A clinical photograph of a skin lesion · a subject 28 years old: 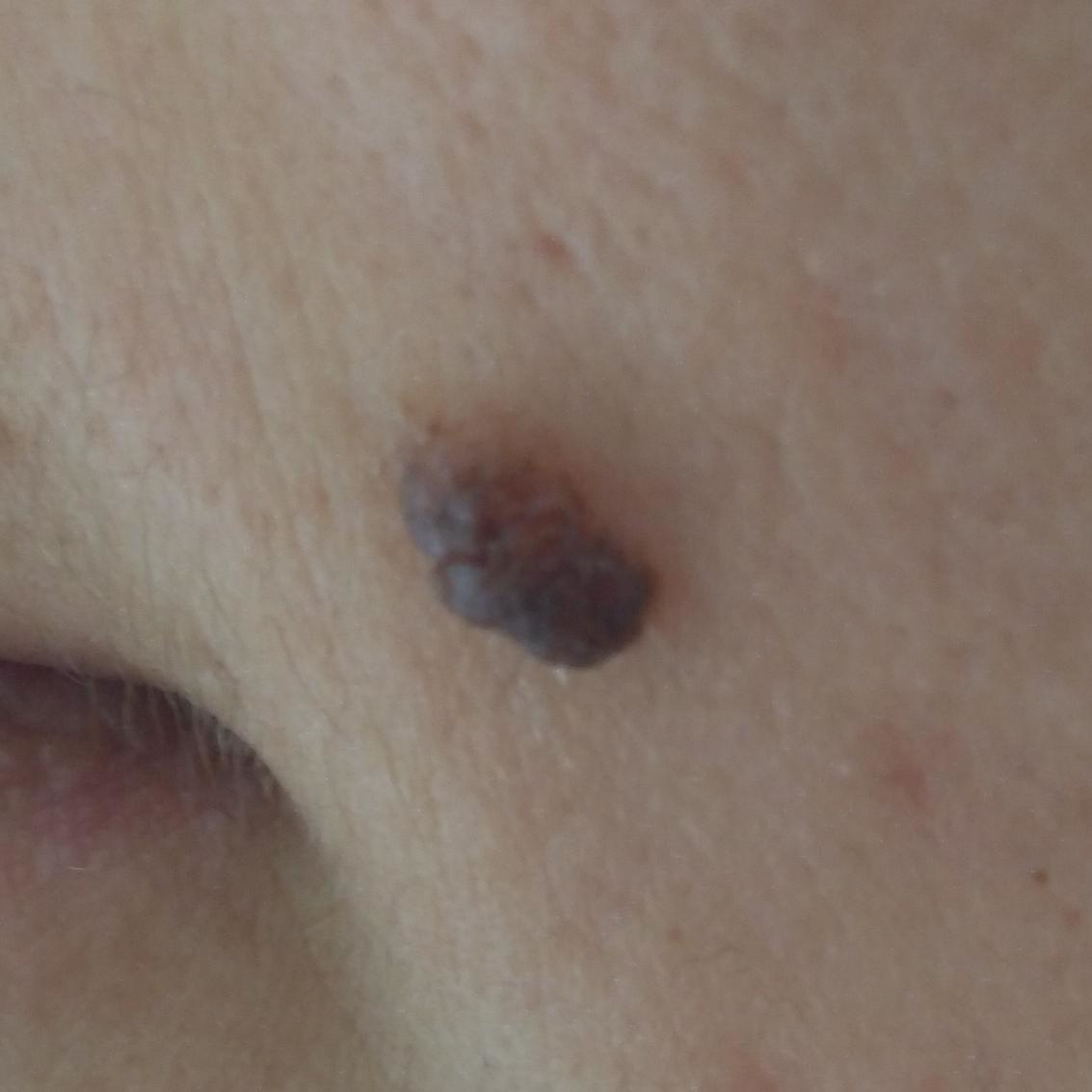Summary: The lesion involves the face. The patient describes that the lesion has grown and is elevated. Conclusion: The diagnostic impression was a benign lesion — a nevus.